Located on the back of the hand, arm, sole of the foot, back of the torso, leg, head or neck, palm, front of the torso and top or side of the foot; the photo was captured at a distance — 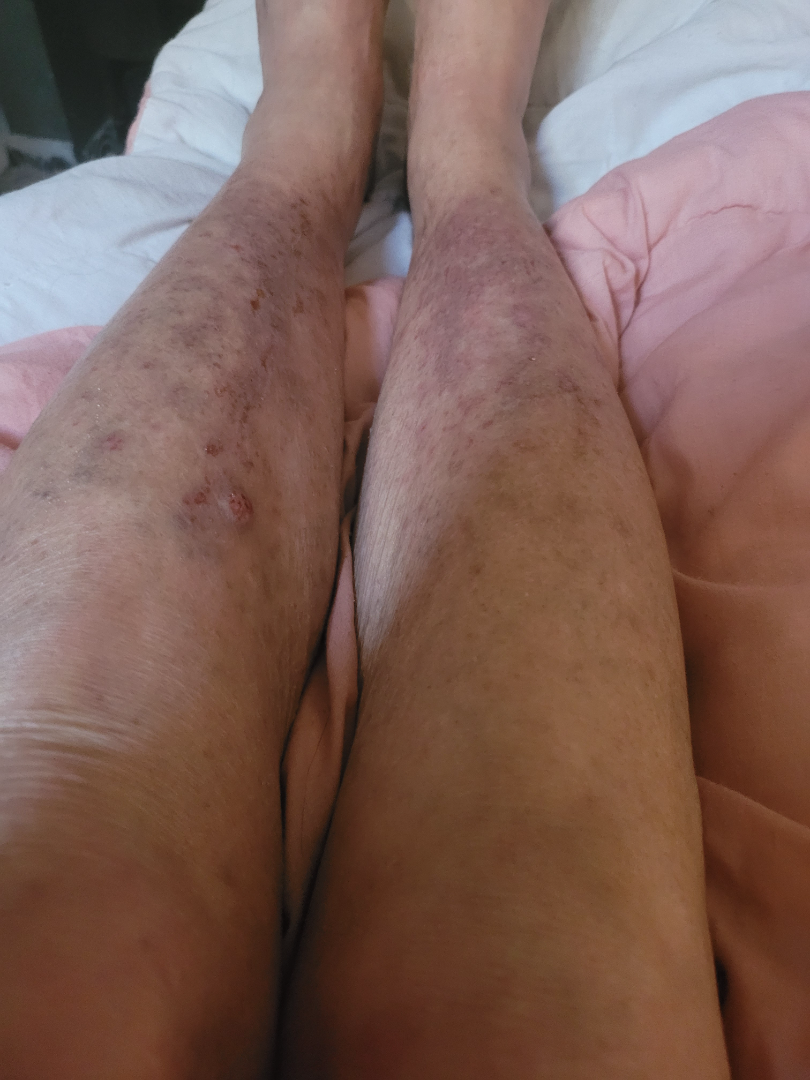- assessment: ungradable on photographic review
- reported symptoms: bothersome appearance
- systemic symptoms: fatigue, fever, shortness of breath and joint pain
- history: more than five years
- described texture: fluid-filled, rough or flaky and raised or bumpy
- patient's own categorization: a rash